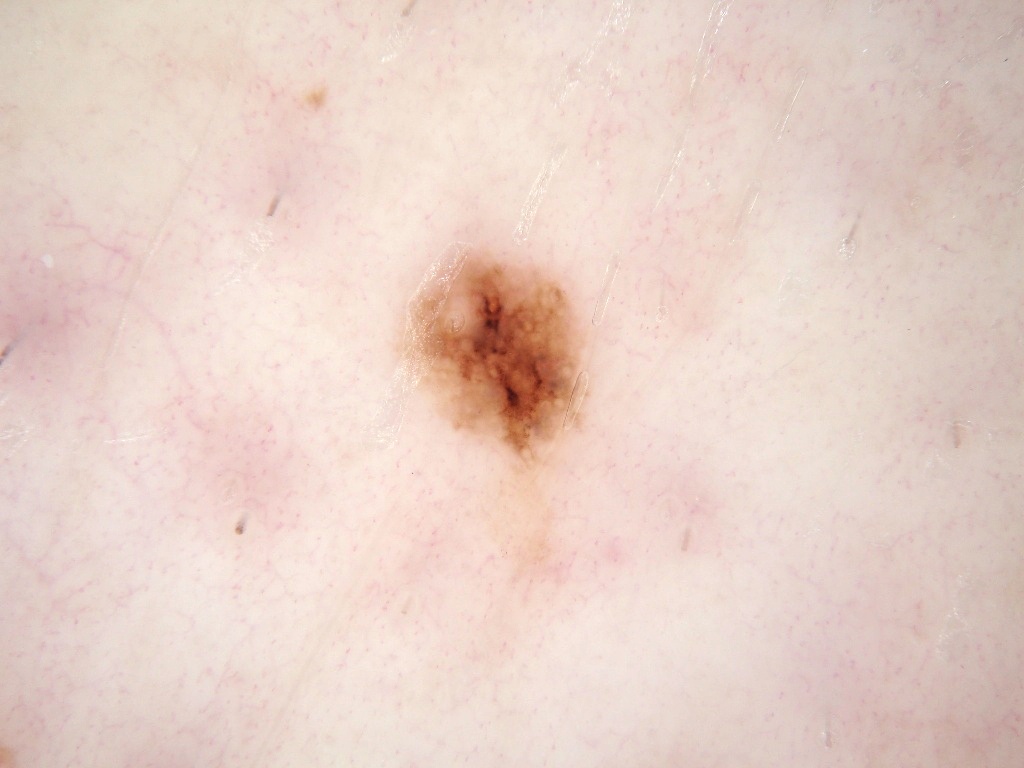  image:
    modality: dermoscopy
  lesion_location:
    bbox_xyxy:
      - 406
      - 248
      - 587
      - 477
  dermoscopic_features:
    present:
      - pigment network
    absent:
      - globules
      - negative network
      - milia-like cysts
      - streaks
  diagnosis:
    name: melanoma
    malignancy: malignant
    lineage: melanocytic
    provenance: histopathology